Fitzpatrick skin type VI · a close-up photograph:
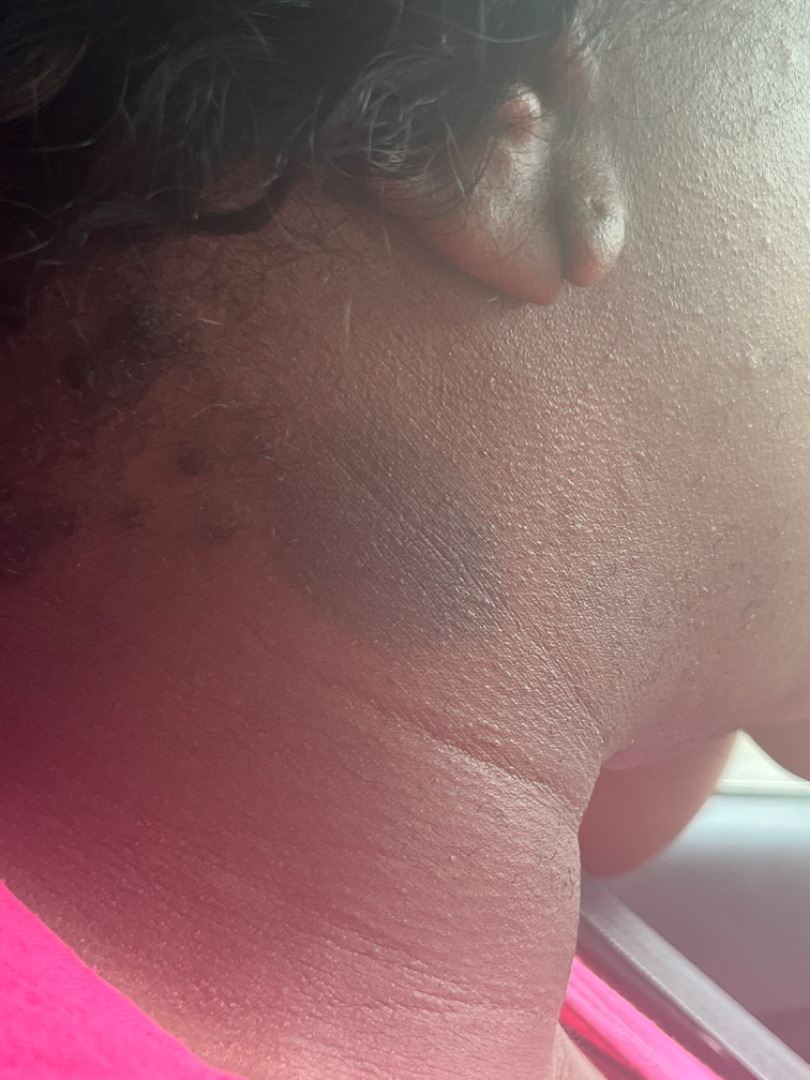Most likely Drug Rash; an alternative is Post-Inflammatory hyperpigmentation.